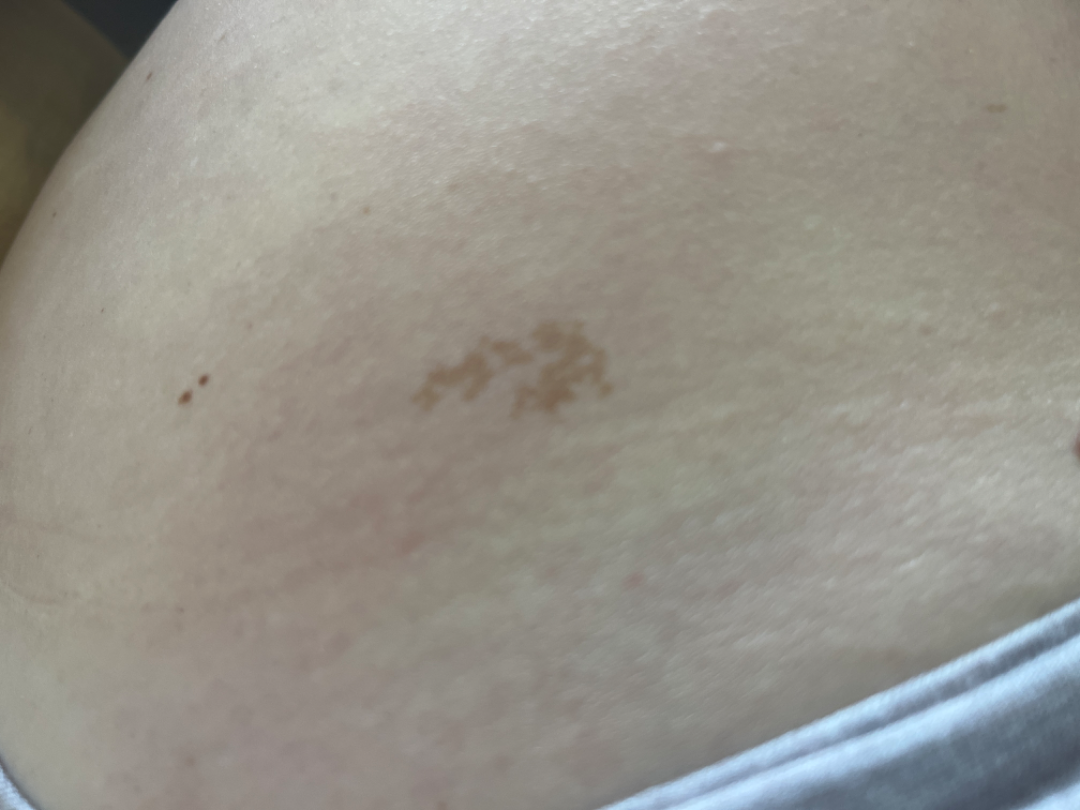Q: What was the assessment?
A: could not be assessed
Q: Constitutional symptoms?
A: none reported
Q: How long has this been present?
A: since childhood
Q: Who is the patient?
A: female, age 30–39
Q: Where on the body?
A: leg
Q: How does the patient describe it?
A: a pigmentary problem
Q: What symptoms does the patient report?
A: none reported
Q: Texture?
A: flat
Q: Image view?
A: close-up